A clinical photo of a skin lesion taken with a smartphone.
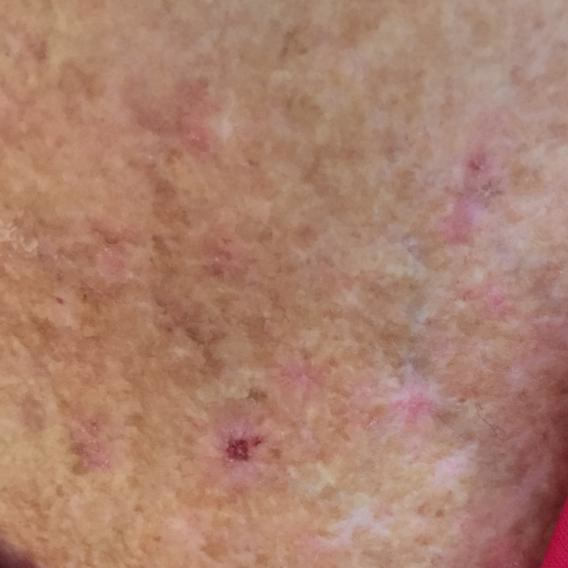Summary:
Per patient report, the lesion has bled and itches.
Impression:
Expert review favored a lesion with uncertain malignant potential — an actinic keratosis.